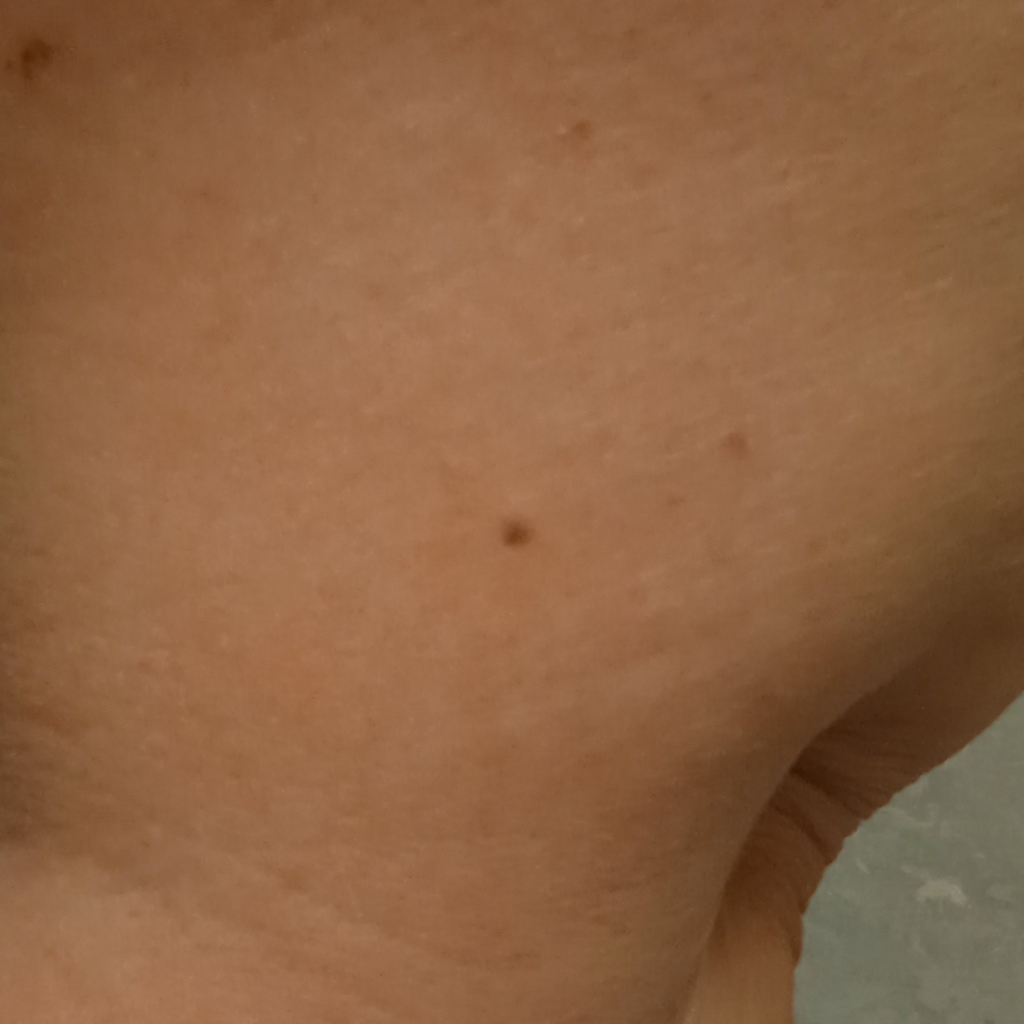Conclusion:
The consensus diagnosis for this lesion was a melanocytic nevus.